The patient considered this a rash; an image taken at a distance; present for less than one week; the patient is a male aged 30–39; the affected area is the arm.
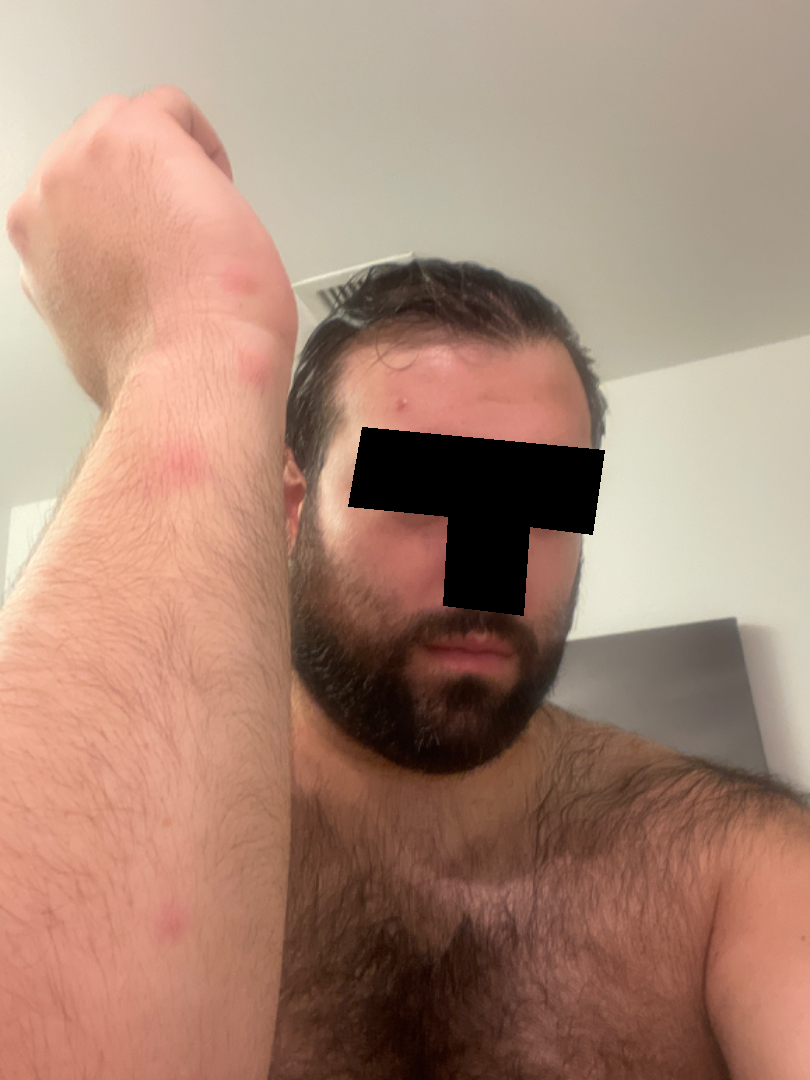assessment = ungradable on photographic review.